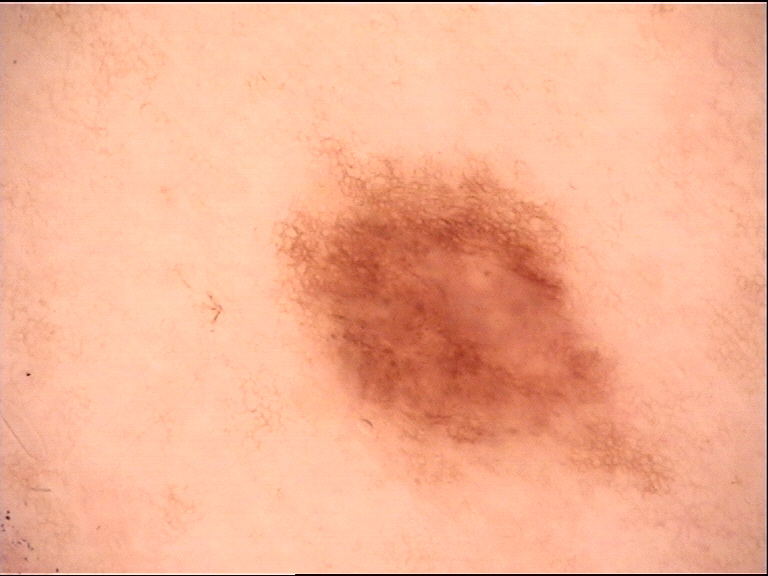Findings:
• modality — dermatoscopy
• class — dysplastic junctional nevus (expert consensus)